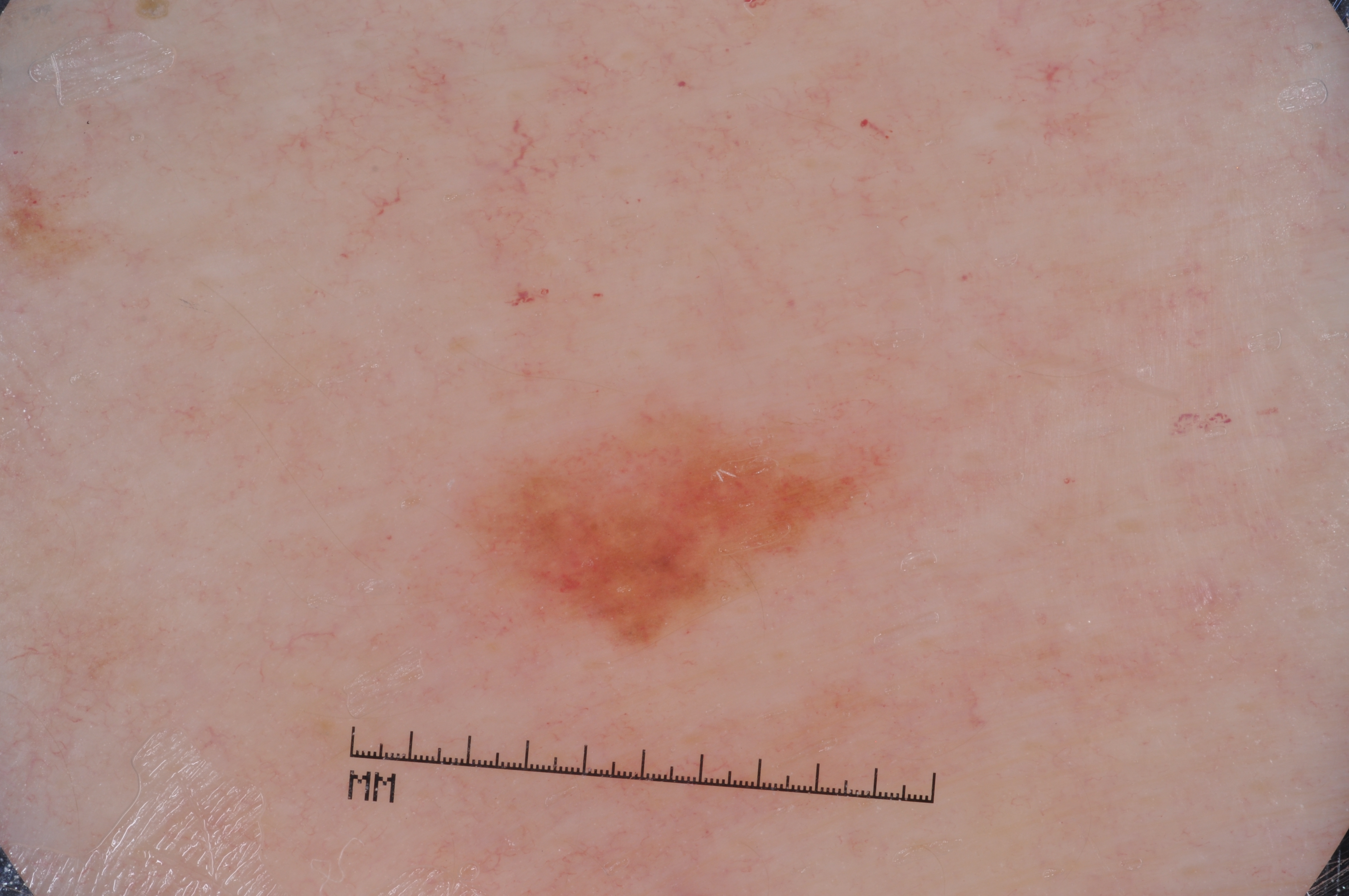• modality — dermoscopy
• patient — female, roughly 80 years of age
• lesion bbox — x1=452, y1=403, x2=898, y2=658
• dermoscopic features not present — milia-like cysts, negative network, pigment network, and streaks
• assessment — a melanoma, a malignancy